A dermoscopic image of a skin lesion.
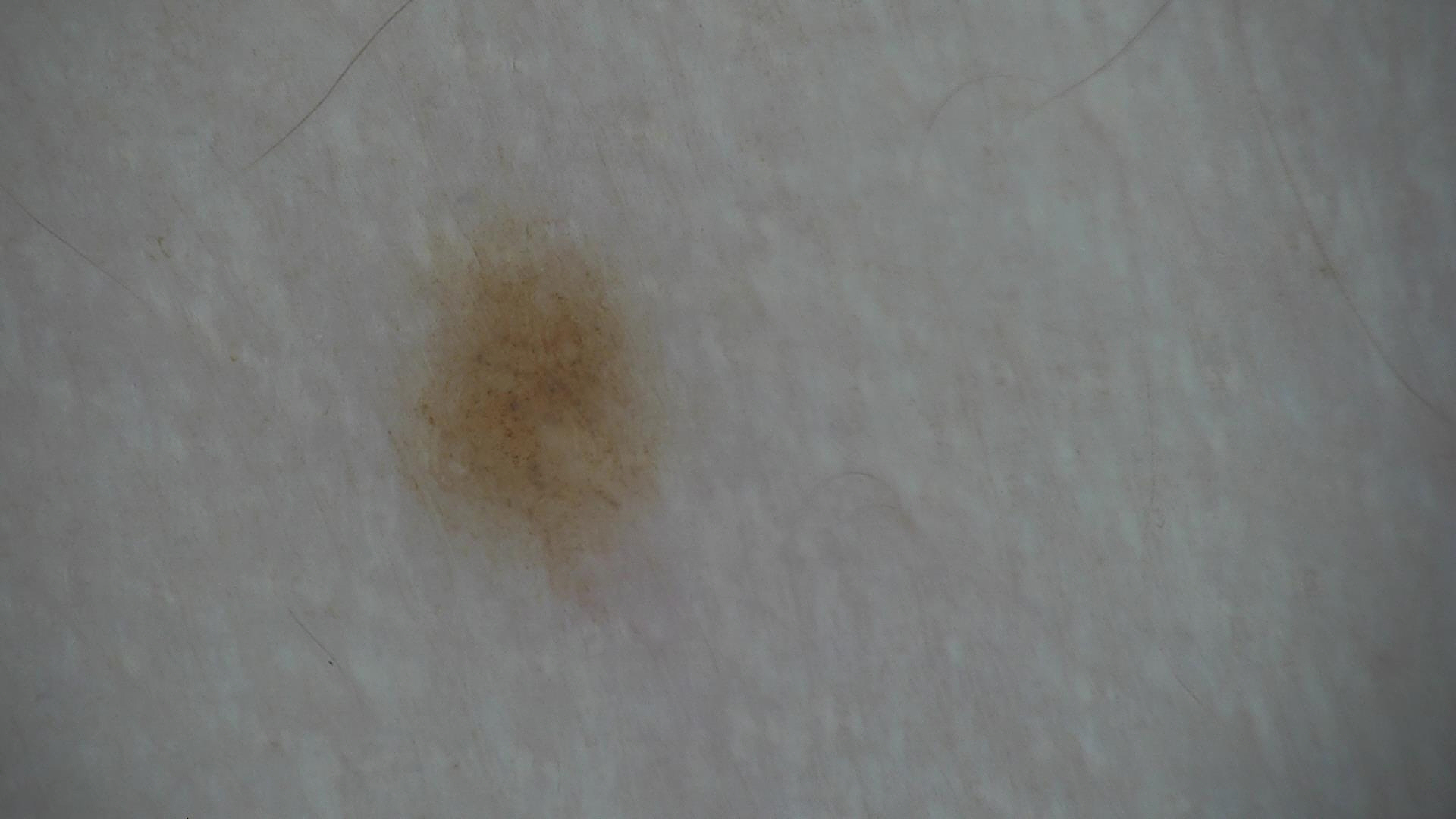Q: What was the diagnostic impression?
A: dysplastic junctional nevus (expert consensus)